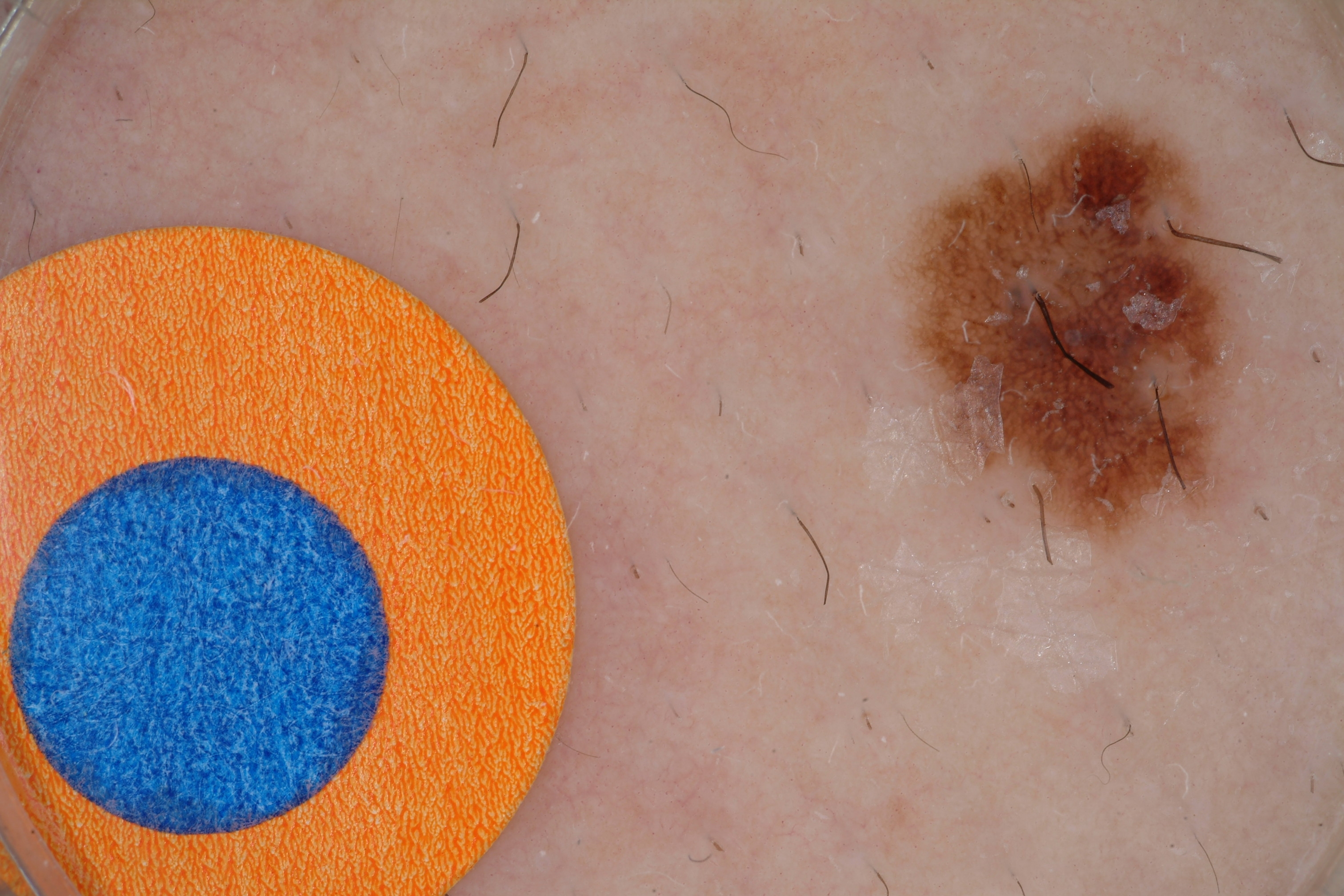A dermoscopic image of a skin lesion.
Dermoscopy demonstrates pigment network.
The lesion occupies roughly 8% of the field.
As (left, top, right, bottom), lesion location: box(913, 107, 1247, 534).
Expert review diagnosed this as a melanocytic nevus.